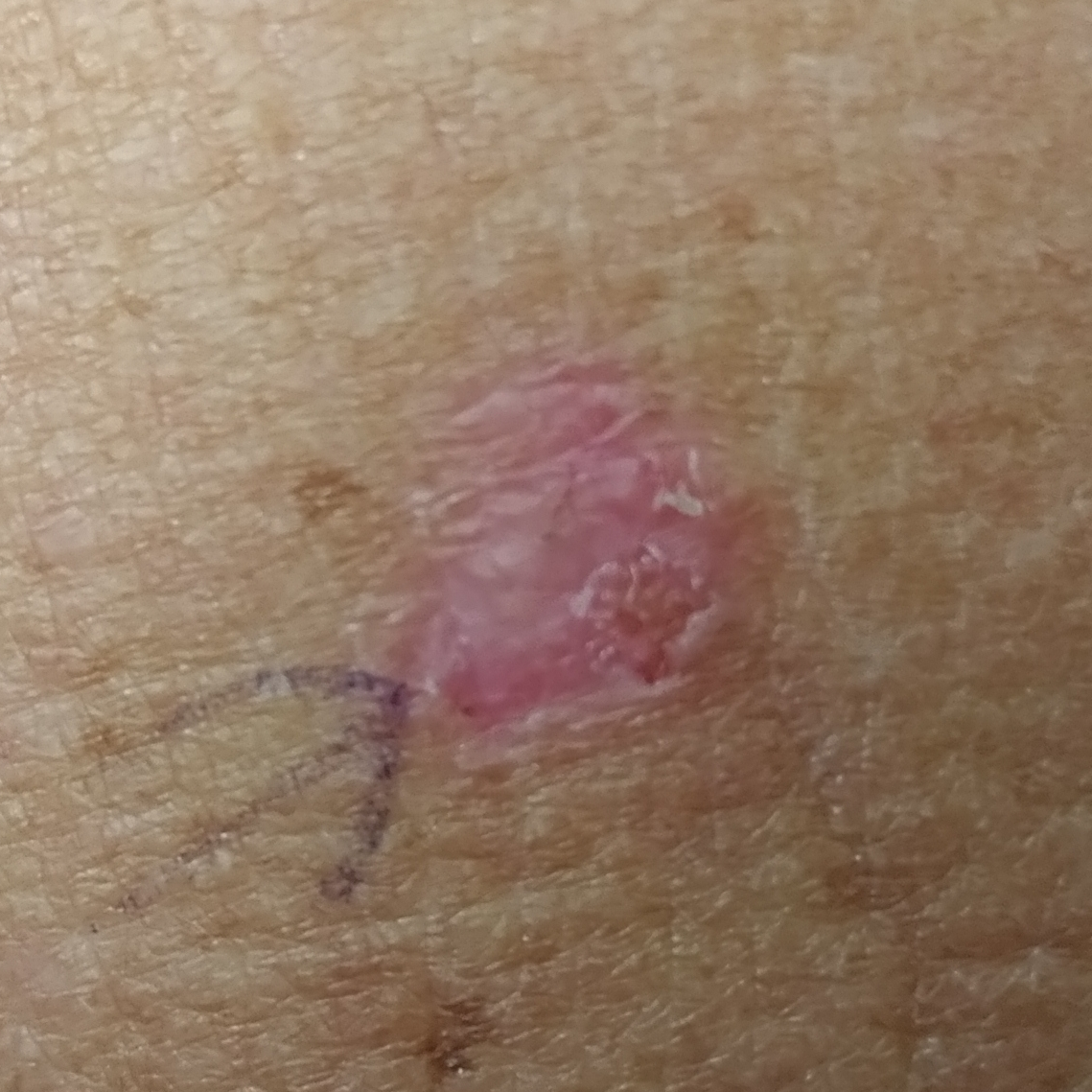Findings:
A smartphone photograph of a skin lesion. Recorded as Fitzpatrick III. The lesion is on the chest. By the patient's account, the lesion has bled, hurts, is elevated, and itches.
Pathology:
Biopsy-confirmed as a basal cell carcinoma.